A dermoscopic close-up of a skin lesion: 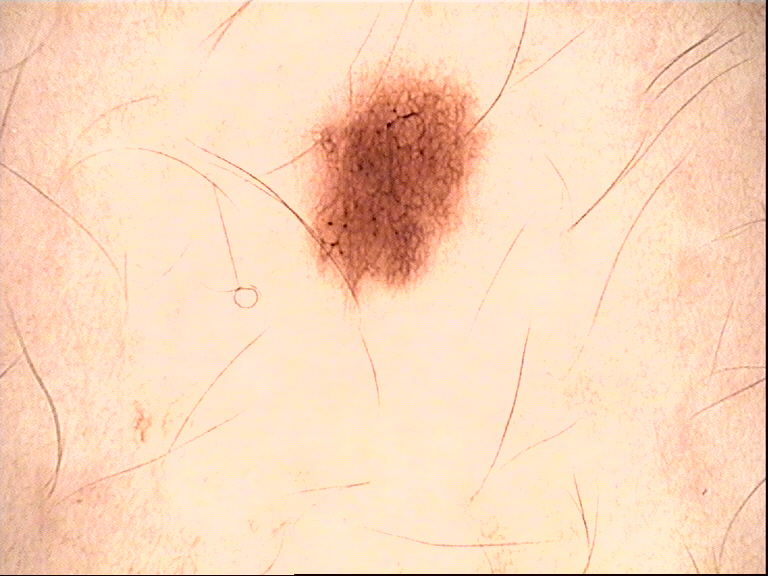diagnostic label: dysplastic junctional nevus (expert consensus).